Dermoscopy of a skin lesion: 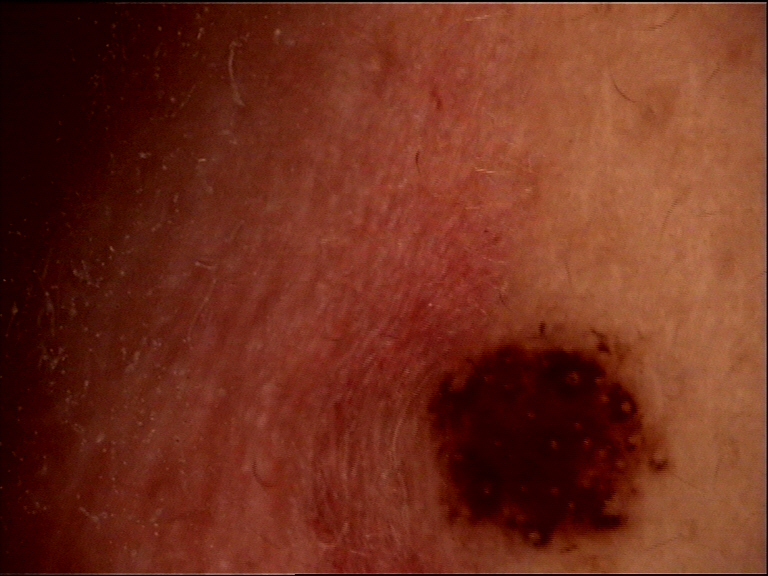lesion_type:
  main_class: banal
  pattern: compound
diagnosis:
  name: congenital compound nevus
  code: ccb
  malignancy: benign
  super_class: melanocytic
  confirmation: expert consensus